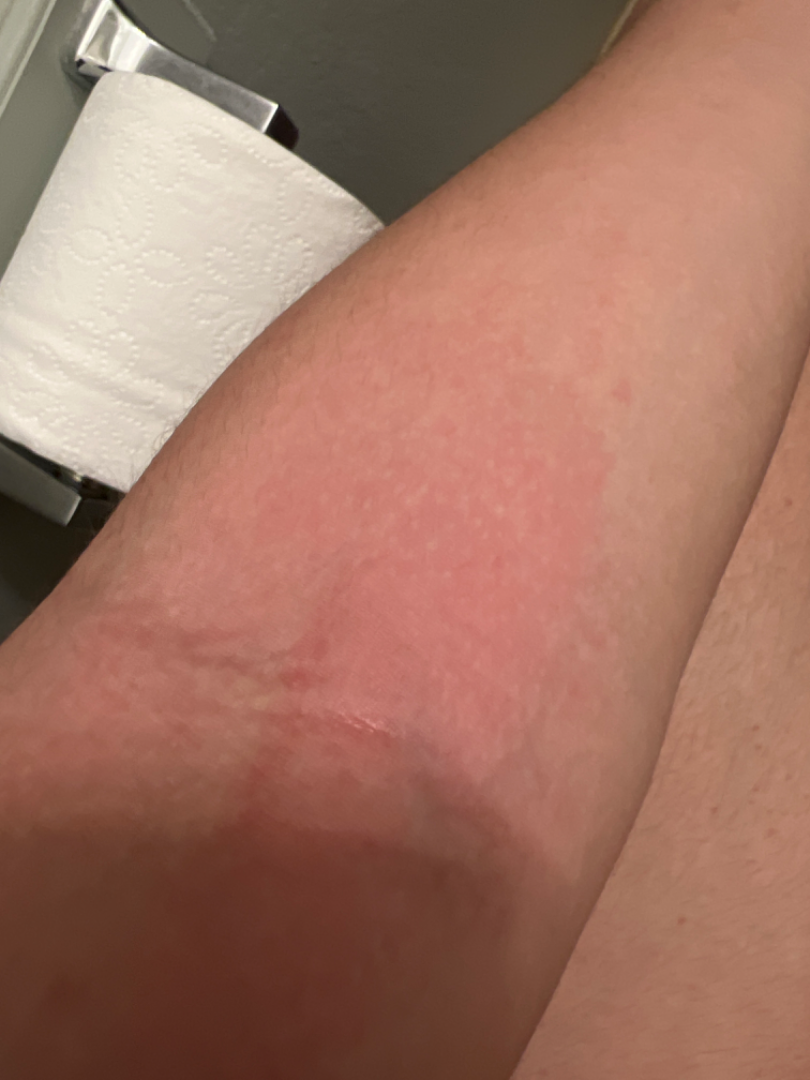Q: Patient demographics?
A: male, age 18–29
Q: What is the affected area?
A: arm
Q: Image view?
A: close-up
Q: What is the dermatologist's impression?
A: most consistent with Eczema; also raised was Urticaria; also consider Irritant Contact Dermatitis; less likely is Acute dermatitis, NOS; a remote consideration is Allergic Contact Dermatitis; lower on the differential is Cellulitis